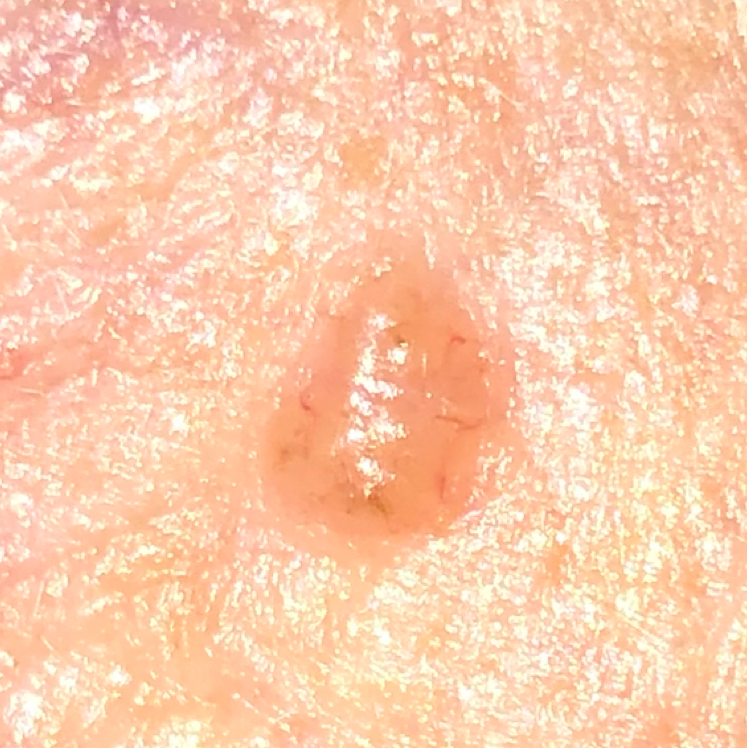Case:
* image · smartphone clinical photo
* patient · female, 49 years of age
* region · the face
* patient-reported symptoms · pain, elevation, itching
* diagnostic label · basal cell carcinoma (biopsy-proven)